A dermoscopic close-up of a skin lesion.
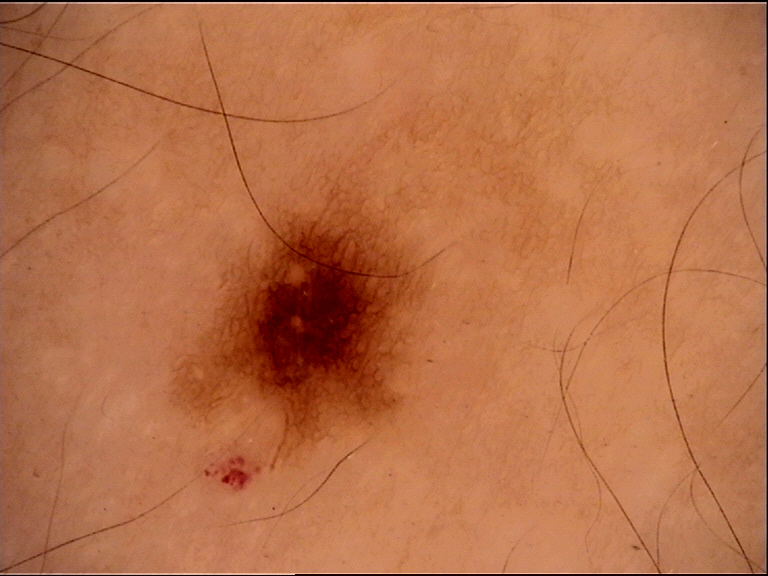This is a banal lesion. Labeled as a junctional nevus.